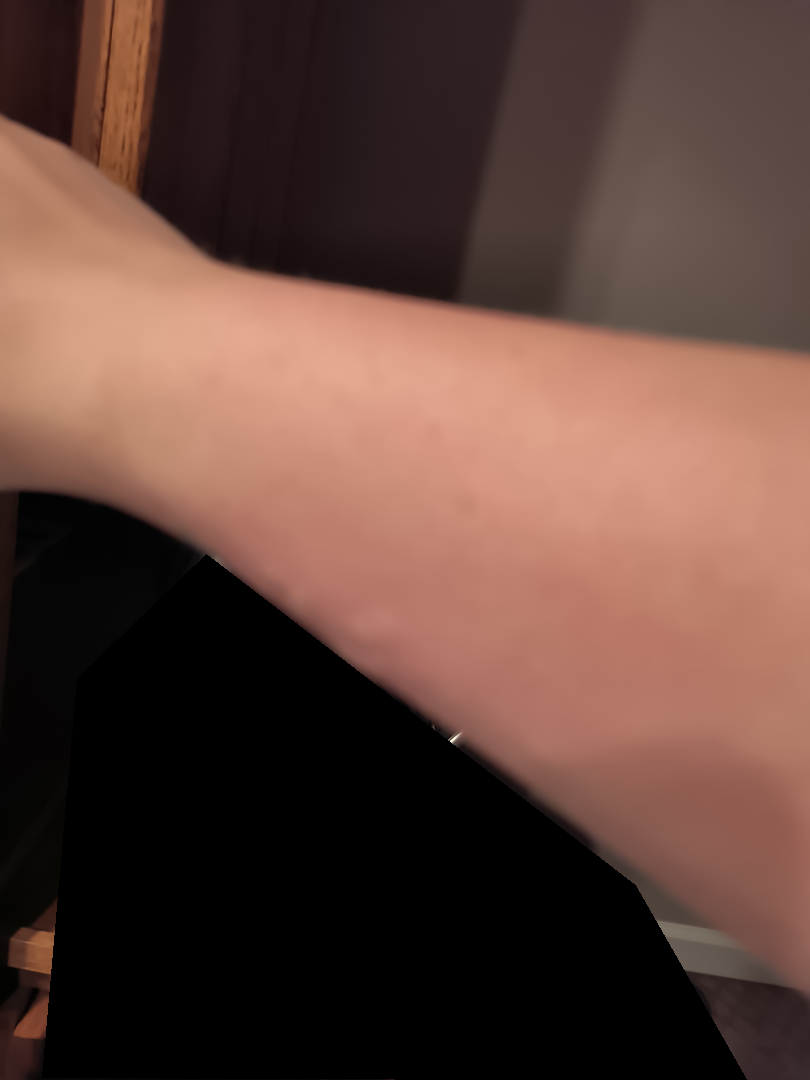Review: Favoring Urticaria; the differential also includes Insect Bite; an alternative is Allergic Contact Dermatitis.